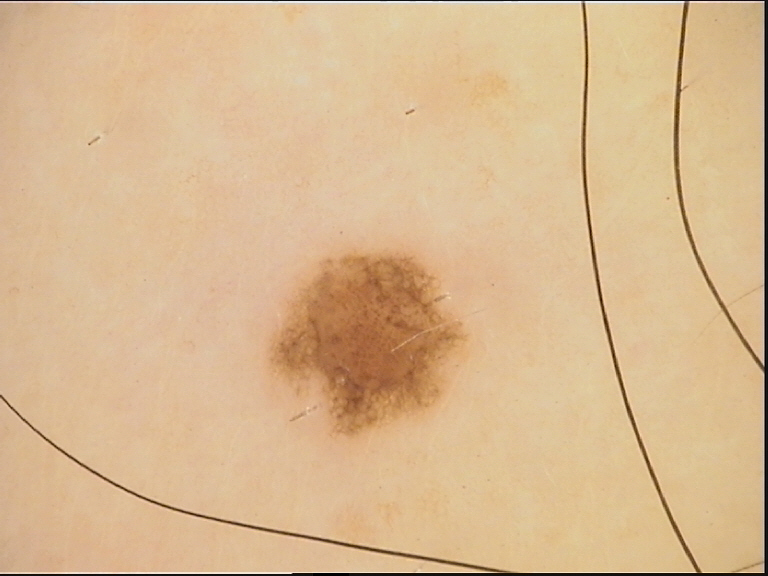Classified as a dysplastic junctional nevus.